The sole of the foot is involved; symptoms reported: pain; the contributor notes the lesion is raised or bumpy; close-up view:
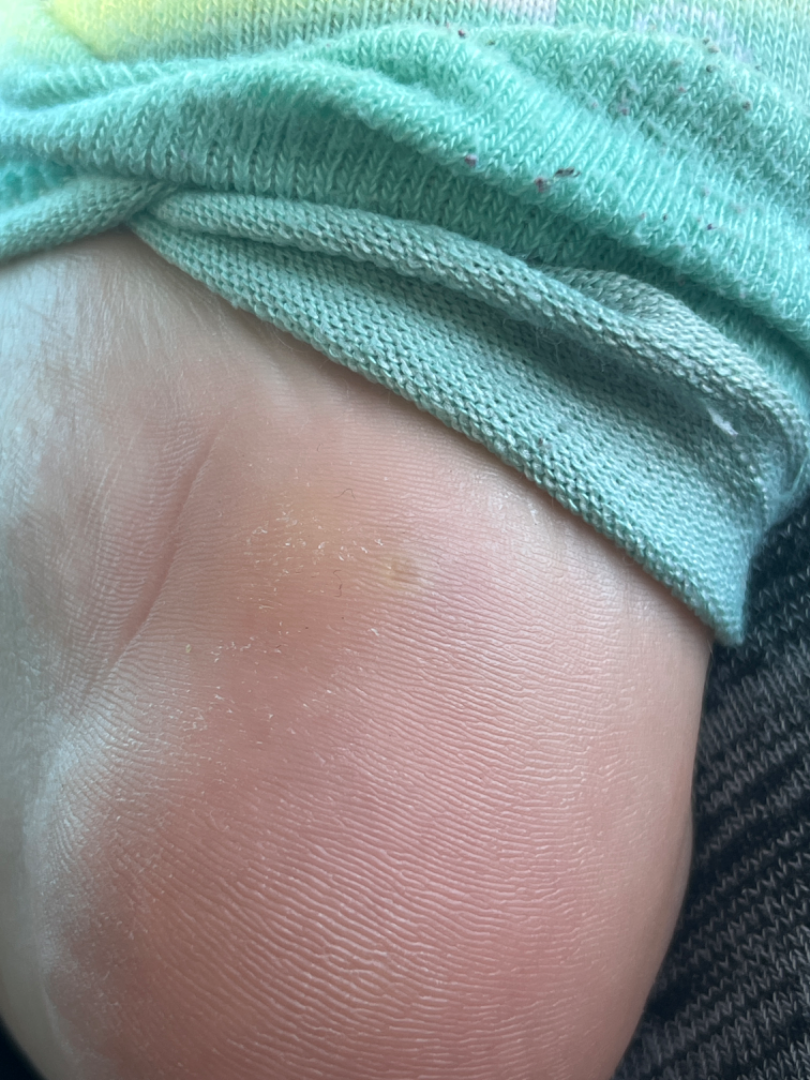differential: Verruca vulgaris